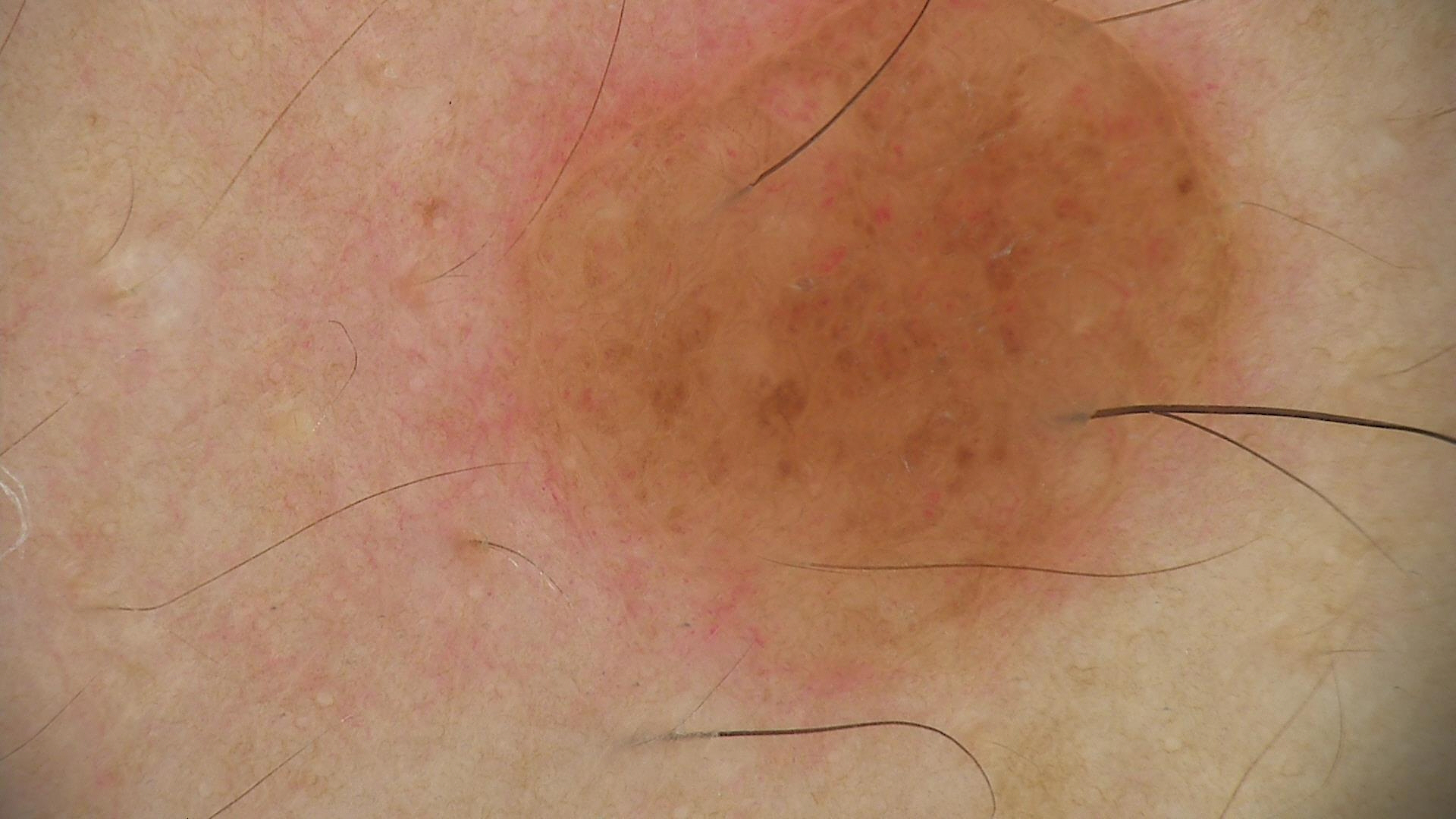Summary:
A dermoscopic close-up of a skin lesion.
Conclusion:
Labeled as a banal lesion — a compound nevus.